Dermoscopy of a skin lesion.
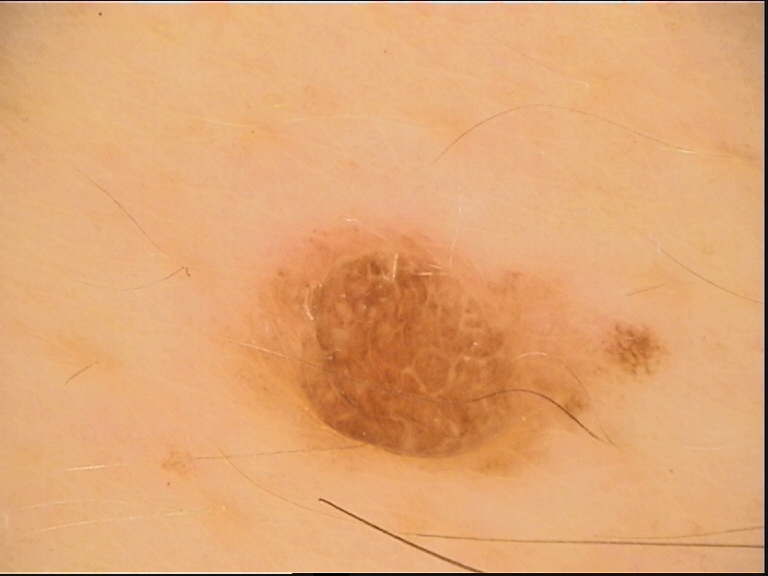Impression: Diagnosed as a compound nevus.